A dermoscopic photograph of a skin lesion: 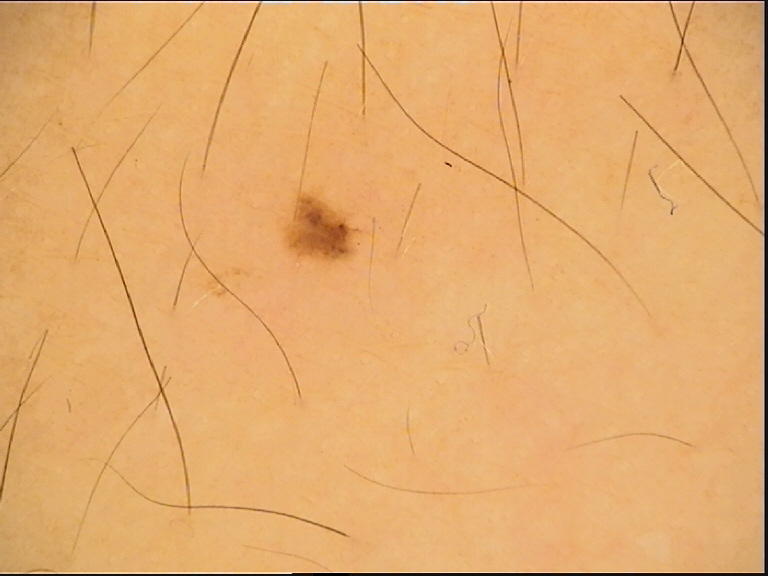Q: What is the diagnosis?
A: dysplastic junctional nevus (expert consensus)